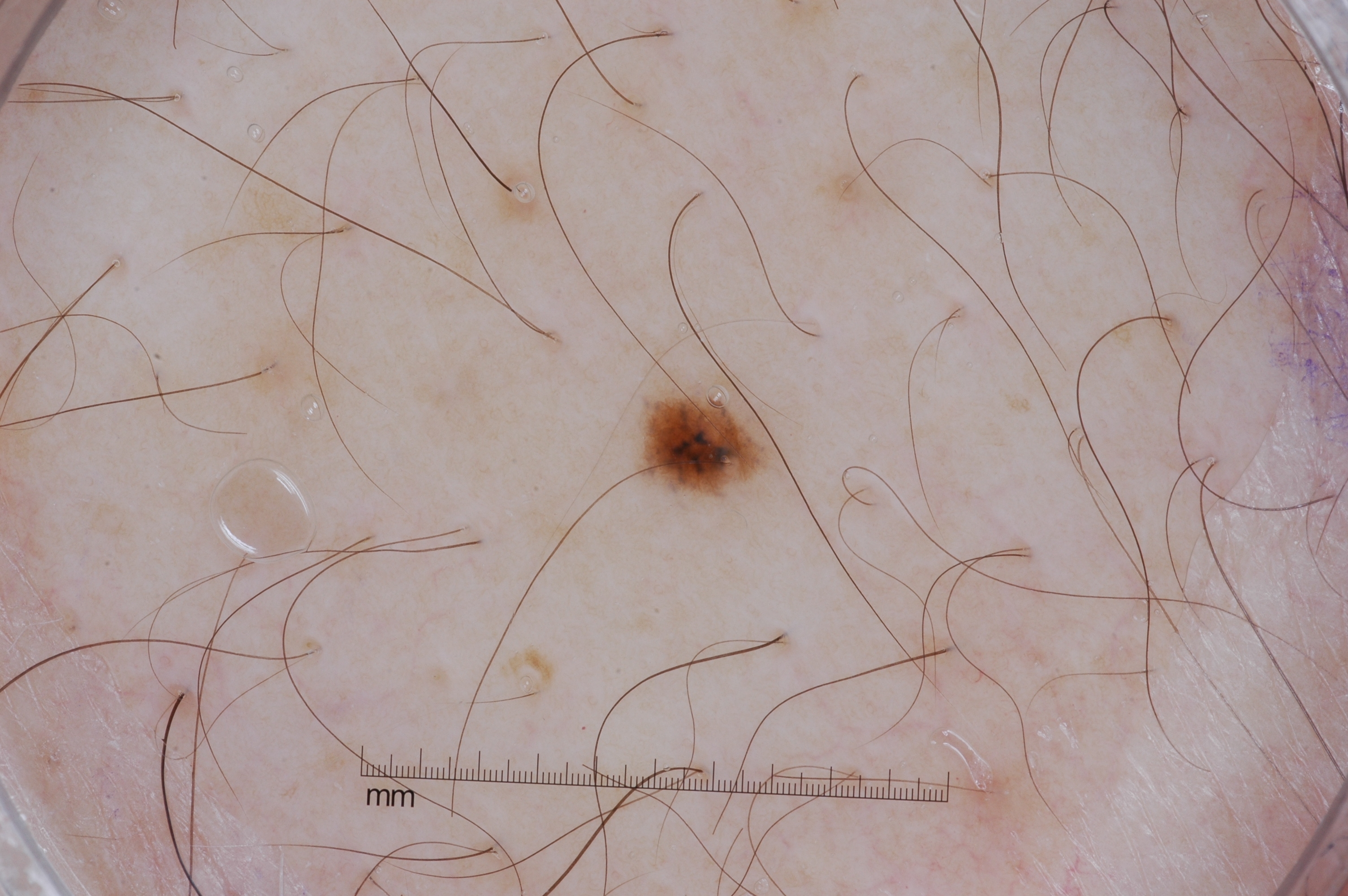{
  "image": {
    "modality": "dermoscopy"
  },
  "patient": {
    "sex": "male",
    "age_approx": 40
  },
  "lesion_extent": "small",
  "dermoscopic_features": {
    "present": [
      "pigment network"
    ],
    "absent": [
      "negative network",
      "milia-like cysts",
      "streaks"
    ]
  },
  "lesion_location": {
    "bbox_xyxy": [
      643,
      392,
      769,
      490
    ]
  },
  "diagnosis": {
    "name": "melanocytic nevus",
    "malignancy": "benign",
    "lineage": "melanocytic",
    "provenance": "clinical"
  }
}